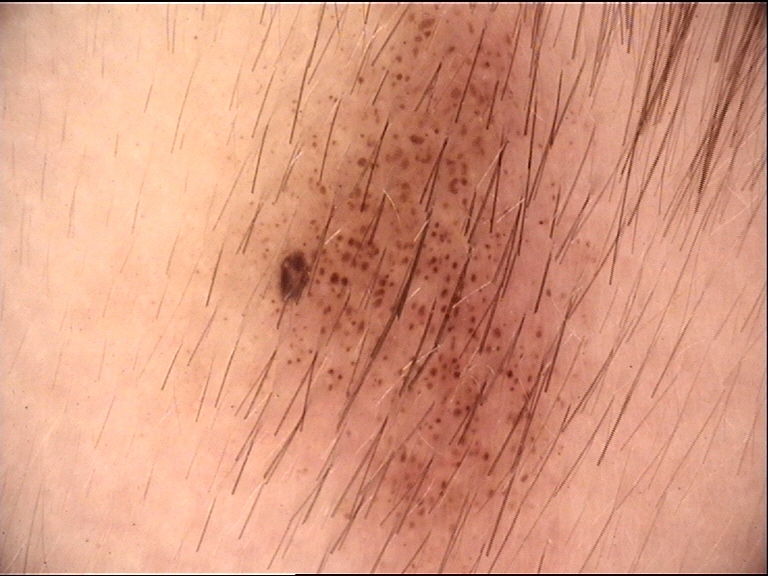{"image": "dermoscopy", "lesion_type": {"main_class": "banal", "pattern": "junctional"}, "diagnosis": {"name": "congenital junctional nevus", "code": "cjb", "malignancy": "benign", "super_class": "melanocytic", "confirmation": "expert consensus"}}